A dermoscopy image of a single skin lesion.
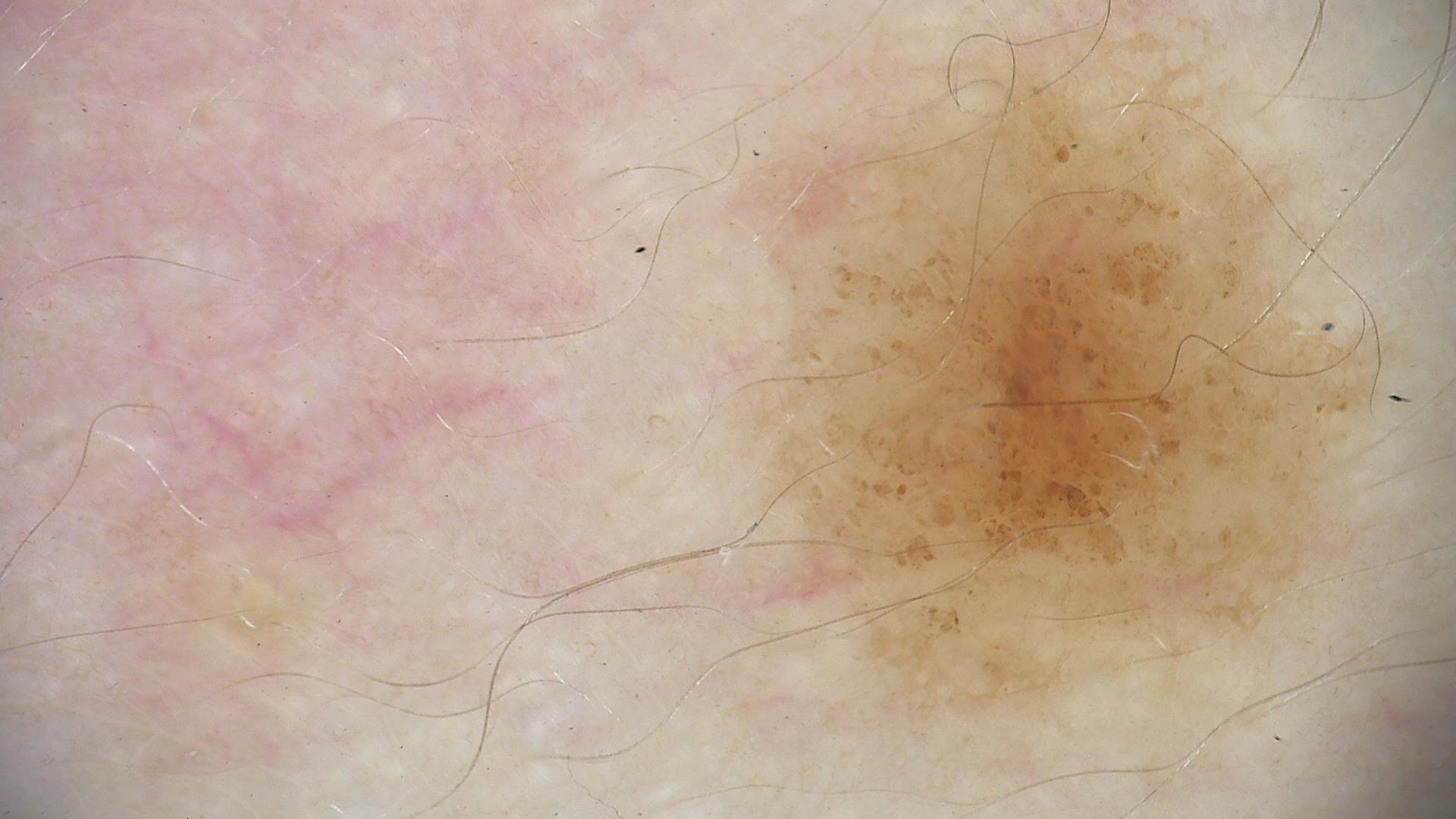Summary:
The architecture is that of a banal lesion.
Conclusion:
Consistent with a compound nevus.